A skin lesion imaged with a dermatoscope.
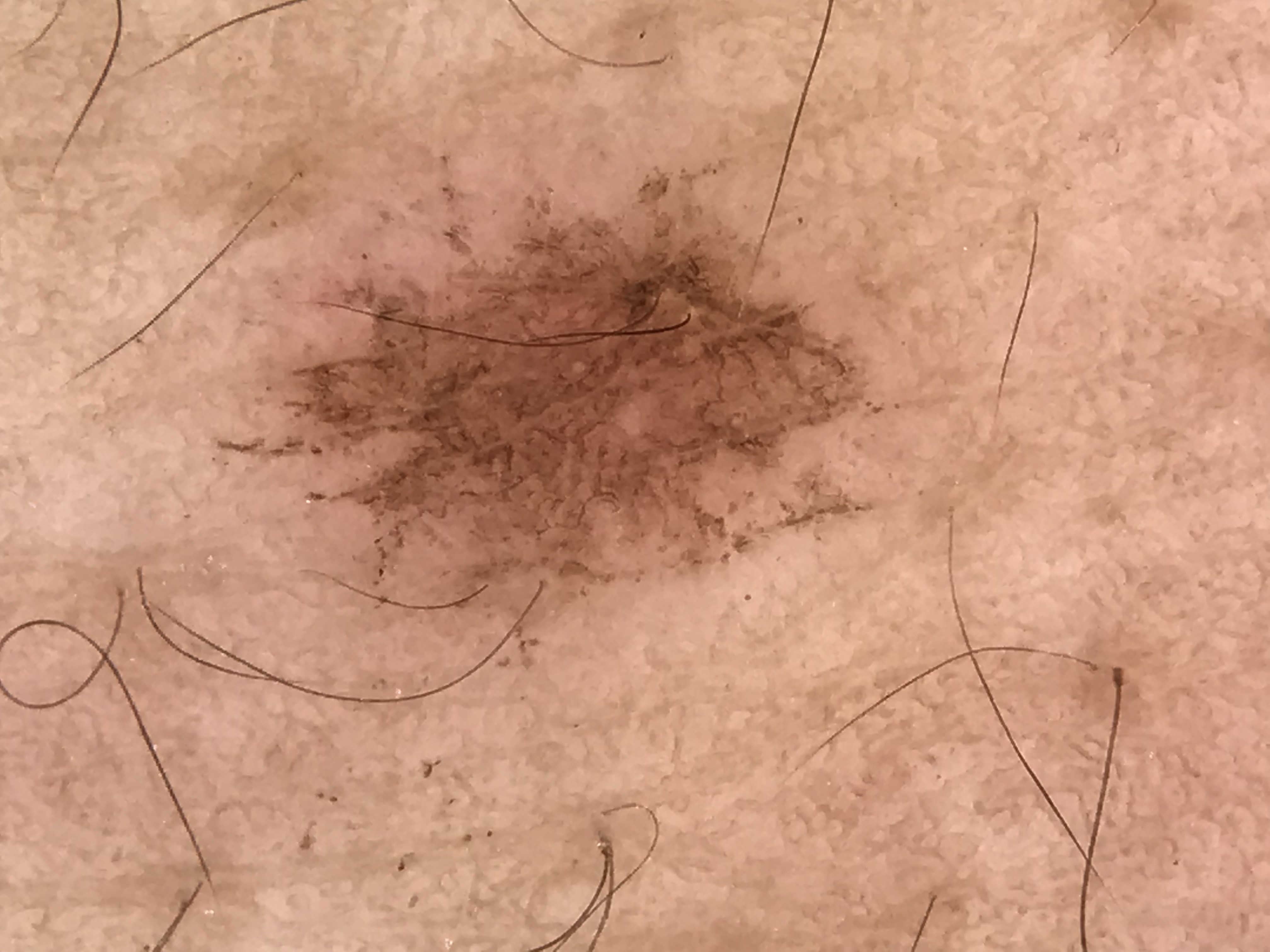Conclusion: The diagnosis was a benign lesion — a lentigo simplex.